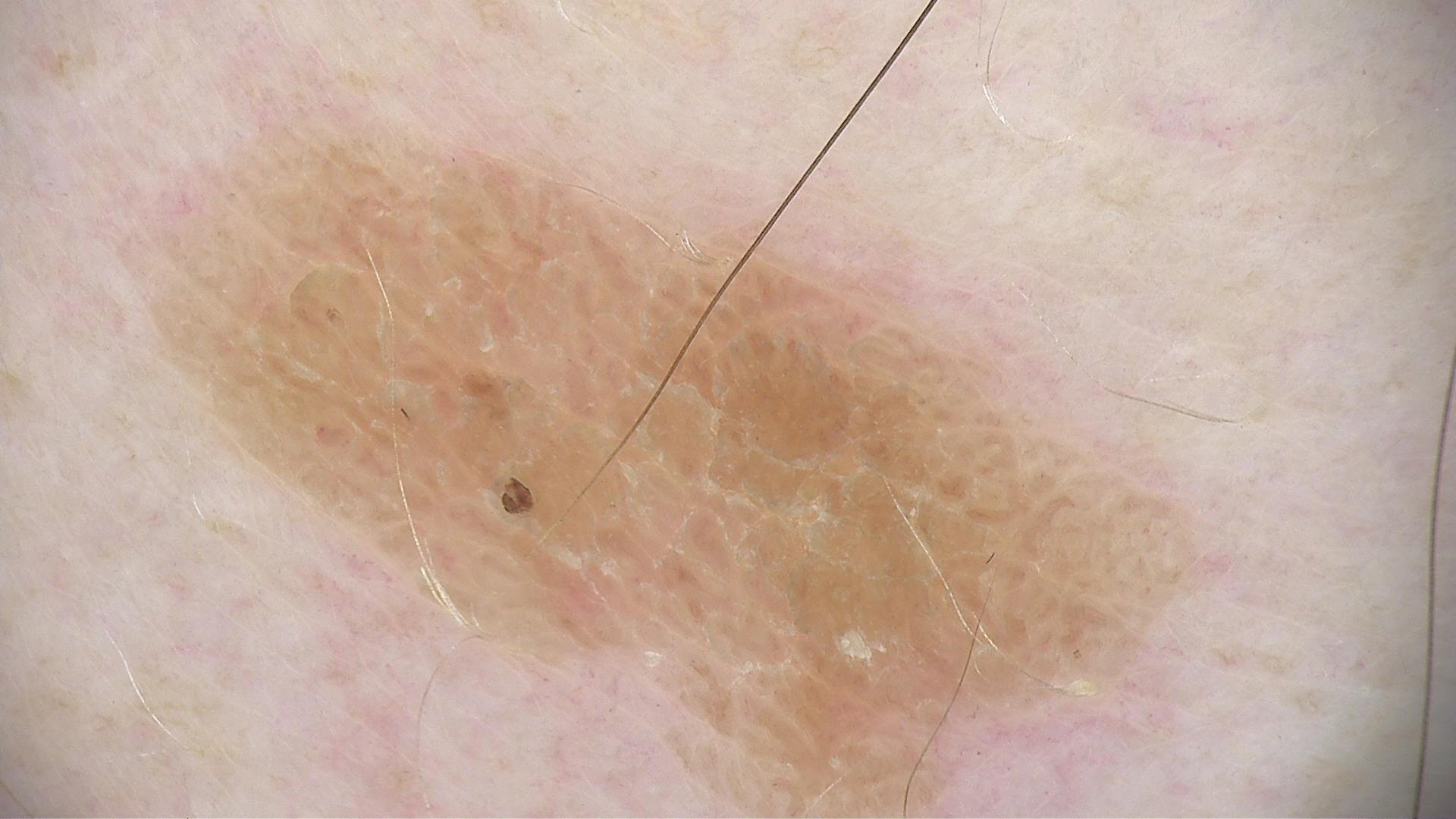A dermatoscopic image of a skin lesion. The diagnosis was a seborrheic keratosis.